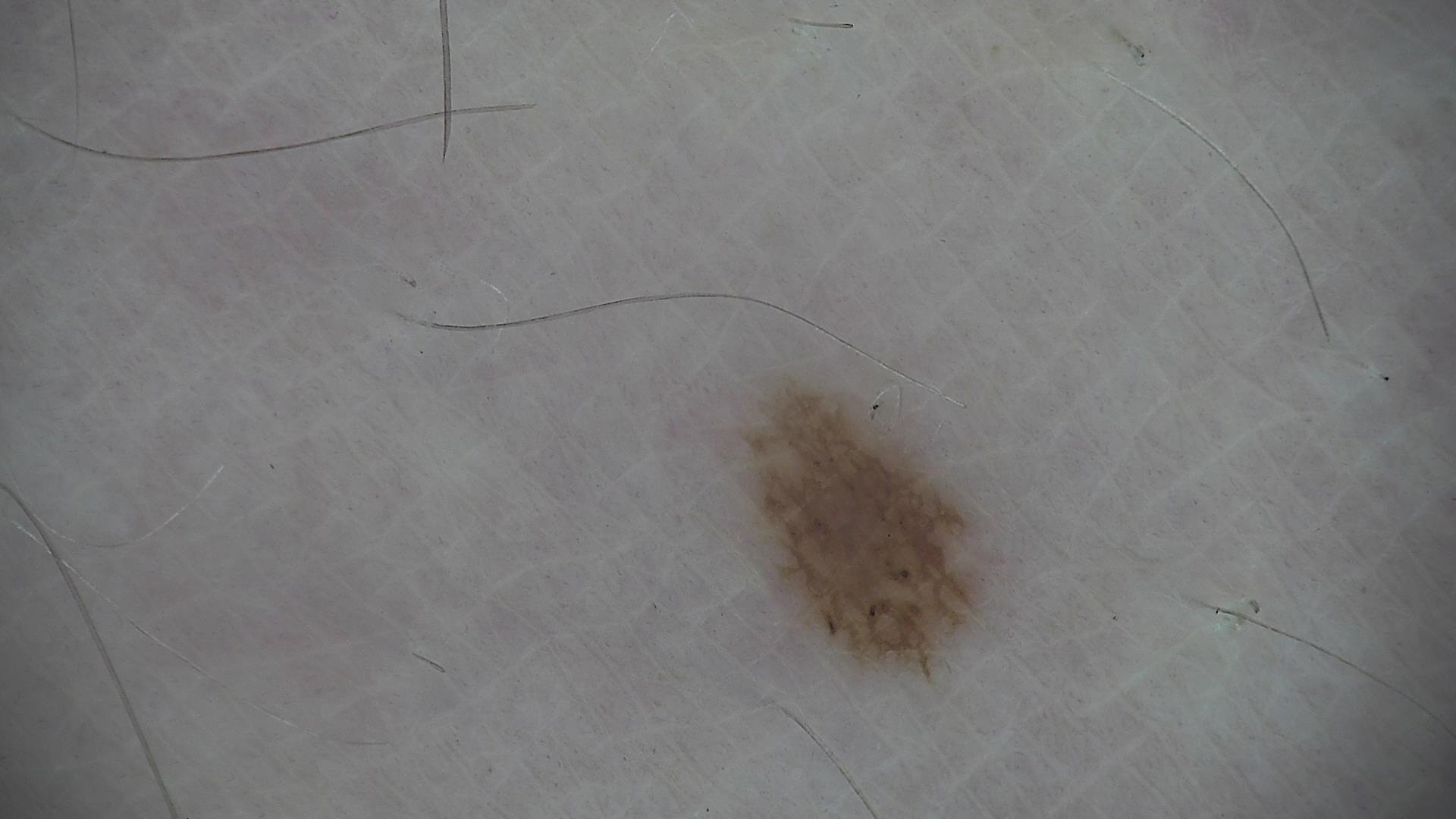image — dermoscopy
assessment — dysplastic junctional nevus (expert consensus)